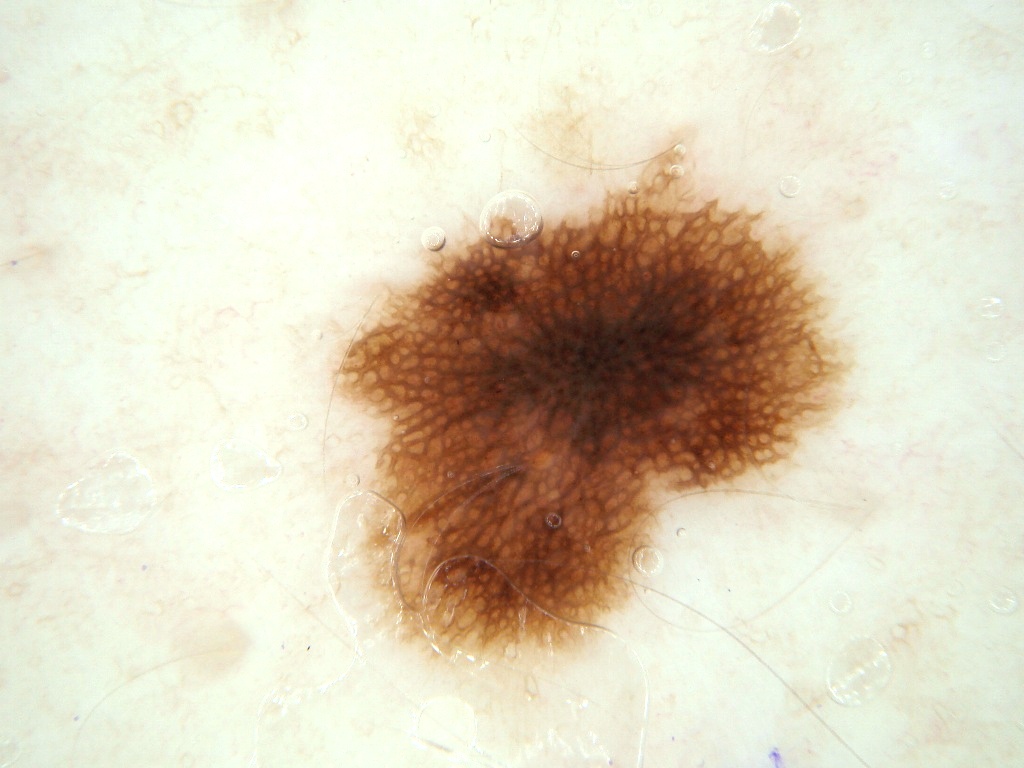The patient is a female aged around 45.
A dermoscopic close-up of a skin lesion.
The lesion spans 340, 149, 842, 653.
Dermoscopic examination shows pigment network, with no milia-like cysts, negative network, streaks, or globules.
Consistent with a melanocytic nevus.